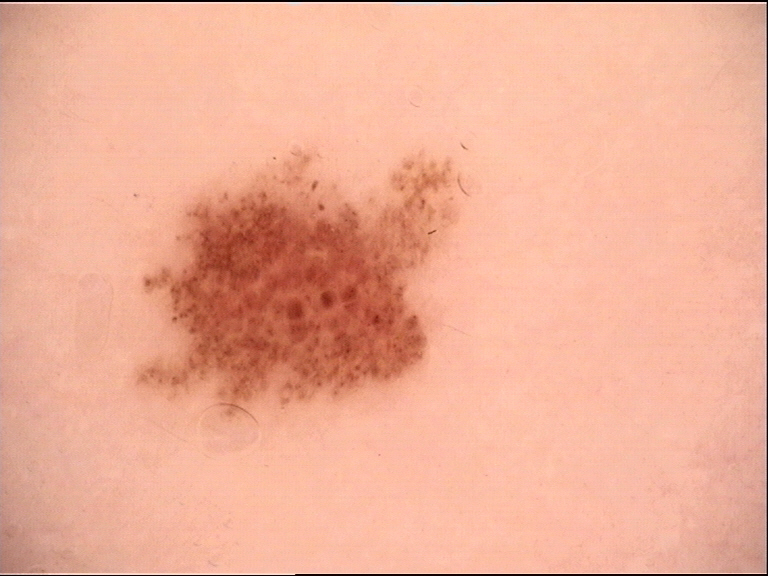Dermoscopy of a skin lesion. Labeled as a benign lesion — a dysplastic junctional nevus.